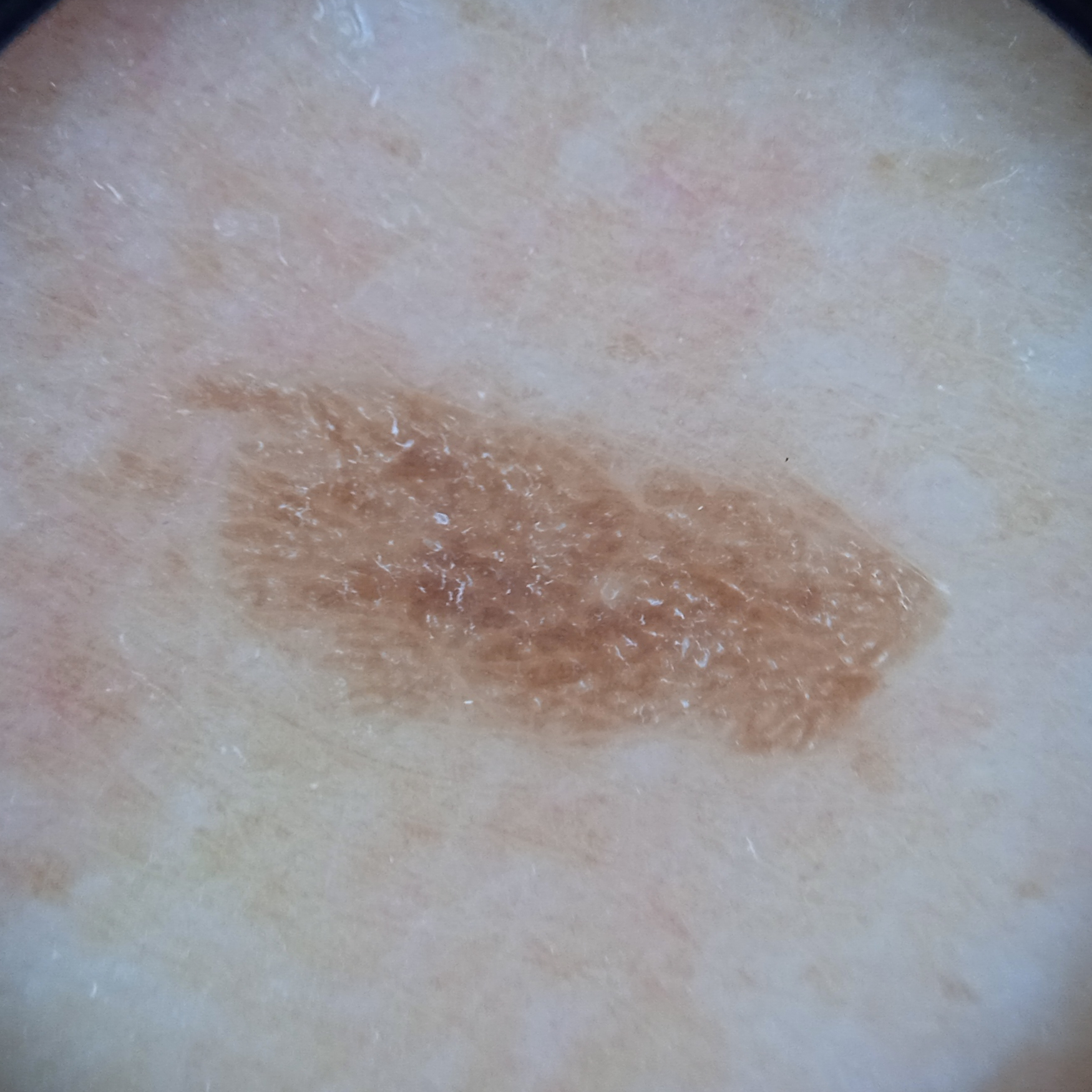referral — research study (no referral diagnosis); nevus count — a moderate number of melanocytic nevi; relevant history — a personal history of skin cancer, a personal history of cancer, no prior organ transplant, no sunbed use; subject — female, aged 75; image type — dermatoscopic image; sun reaction — skin tans without first burning; site — the back; size — 8.4 mm; diagnosis — seborrheic keratosis (dermatologist consensus).